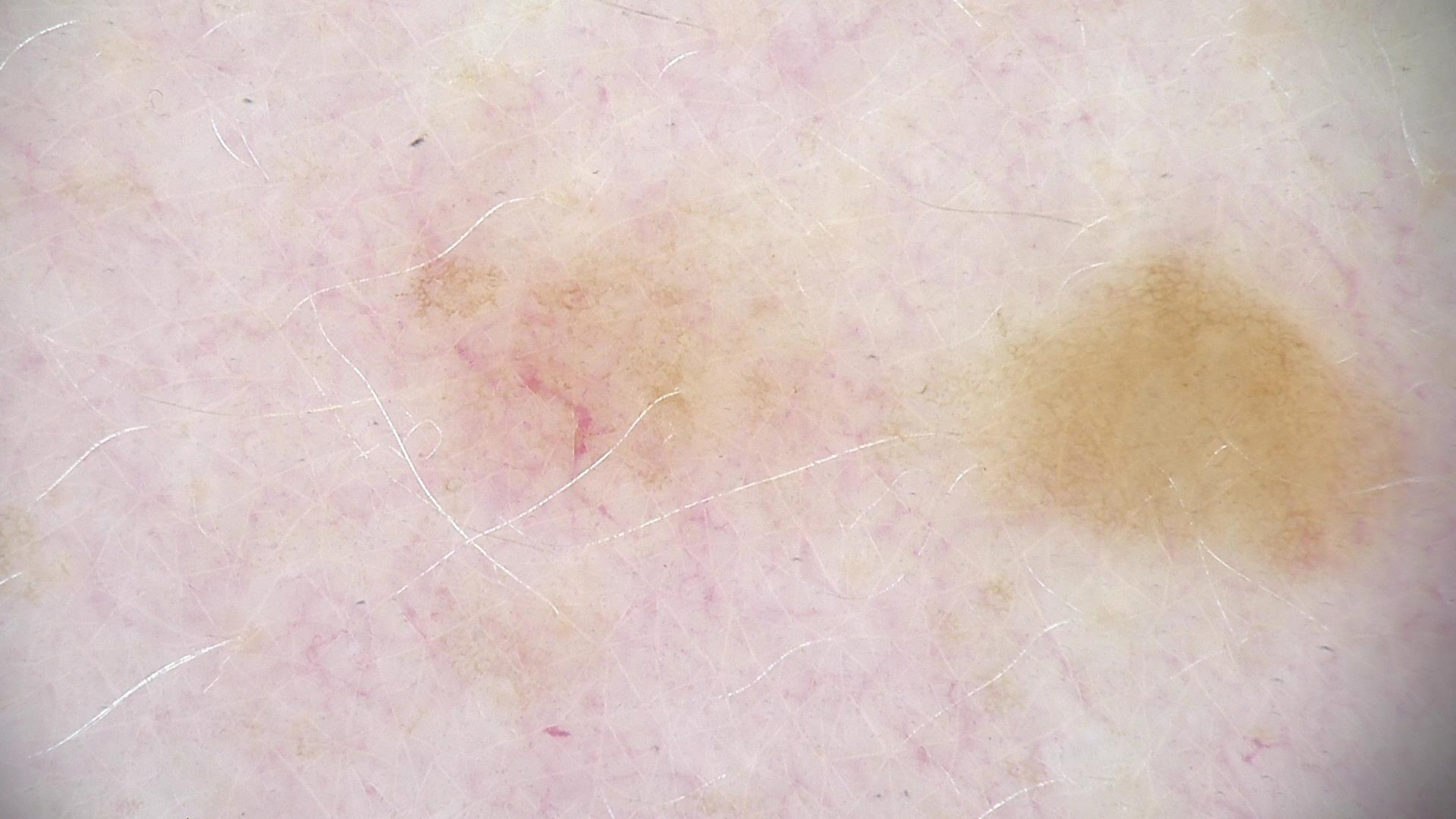- imaging: dermoscopy
- assessment: dysplastic junctional nevus (expert consensus)